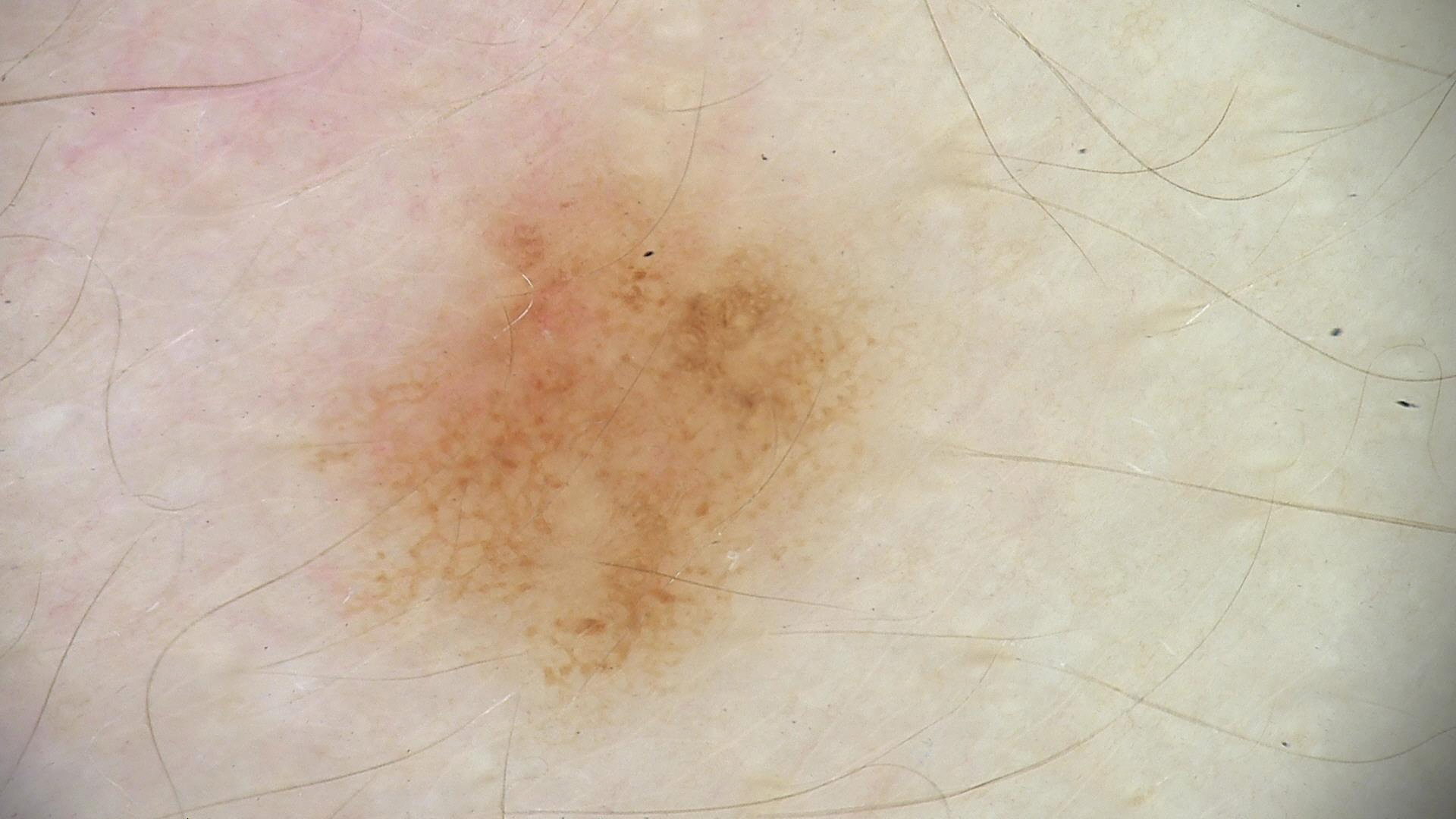<lesion>
<diagnosis>
<name>dysplastic junctional nevus</name>
<code>jd</code>
<malignancy>benign</malignancy>
<super_class>melanocytic</super_class>
<confirmation>expert consensus</confirmation>
</diagnosis>
</lesion>